A macroscopic clinical photograph of a skin lesion; the patient says their skin reddens painfully with sun exposure; few moles overall by the patient's own estimate; a female patient aged 48; acquired for a research image collection, with no referral diagnosis; by self-report, a family history of skin cancer and a history of sunbed use: 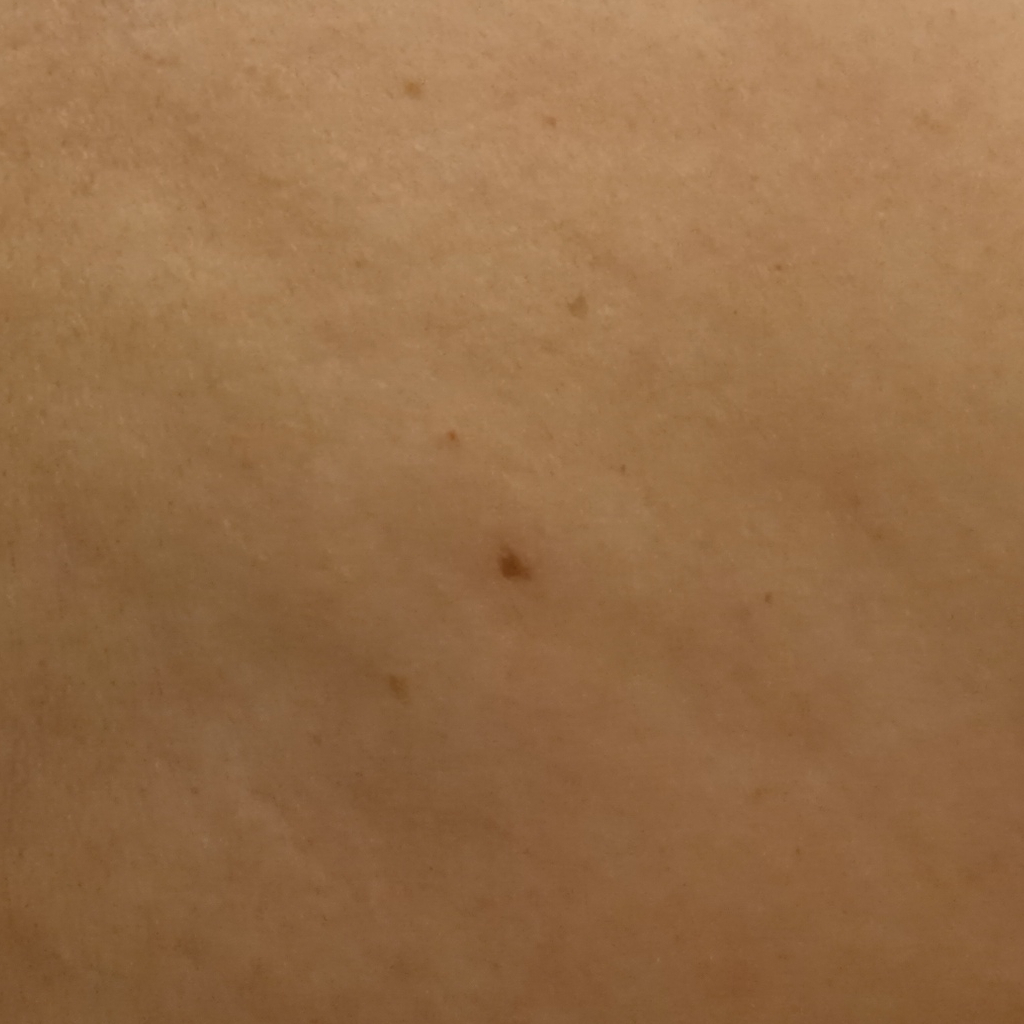Findings:
• location · the back
• size · 3.7 mm
• diagnosis · melanocytic nevus (dermatologist consensus)